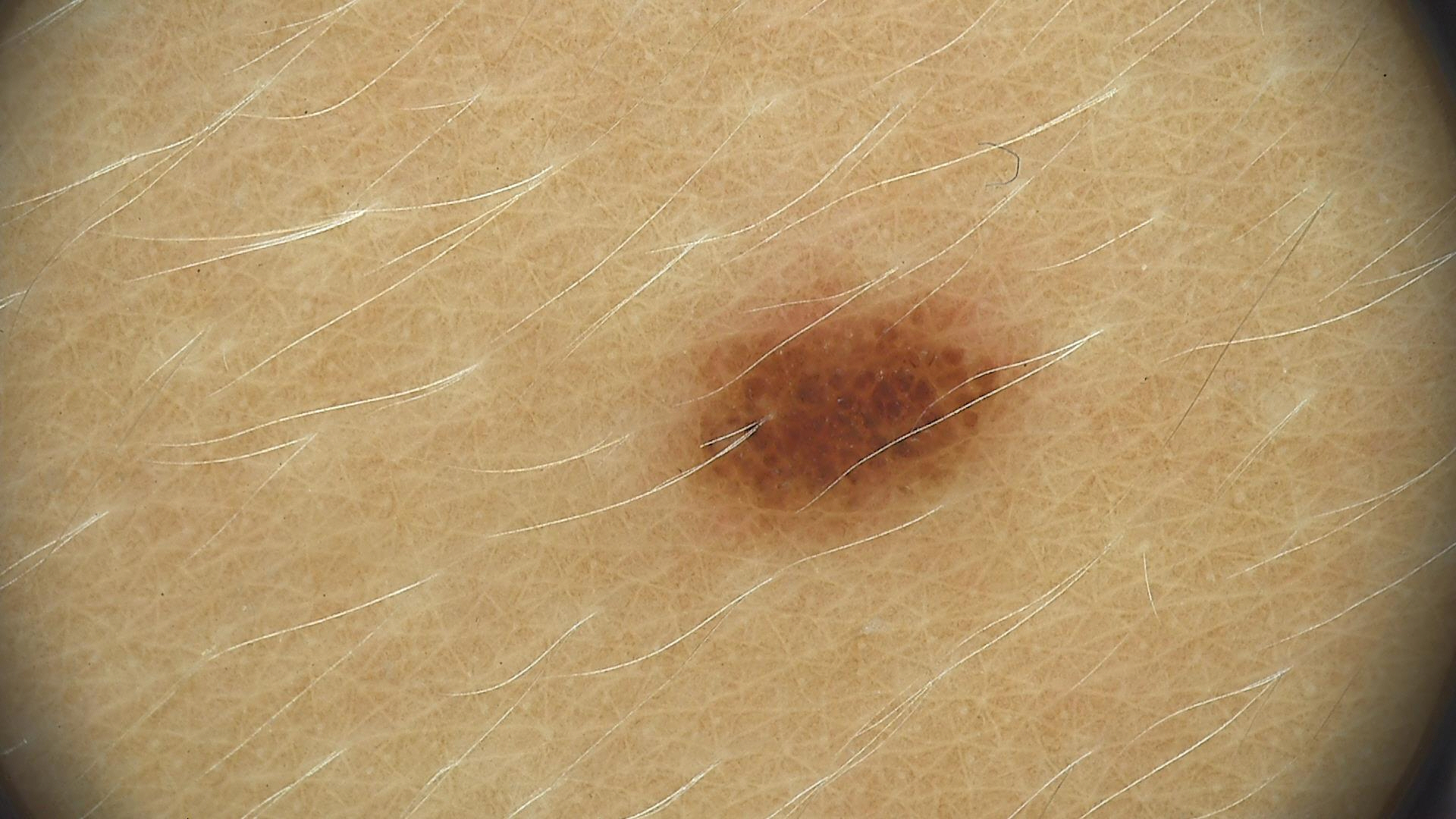Findings:
• label — dysplastic junctional nevus (expert consensus)